A dermoscopic close-up of a skin lesion:
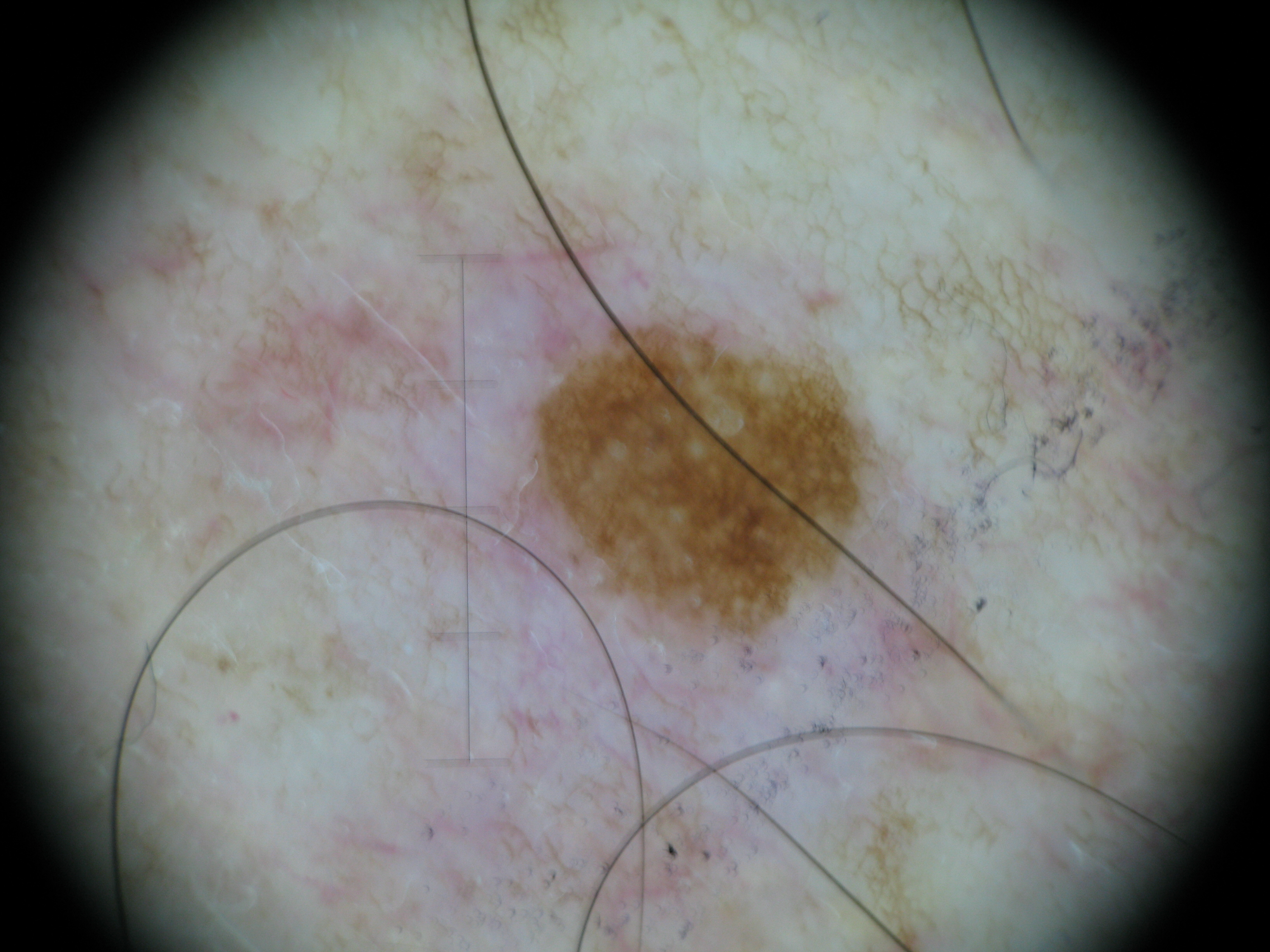category=keratinocytic
diagnosis=seborrheic keratosis (expert consensus)